An image taken at an angle:
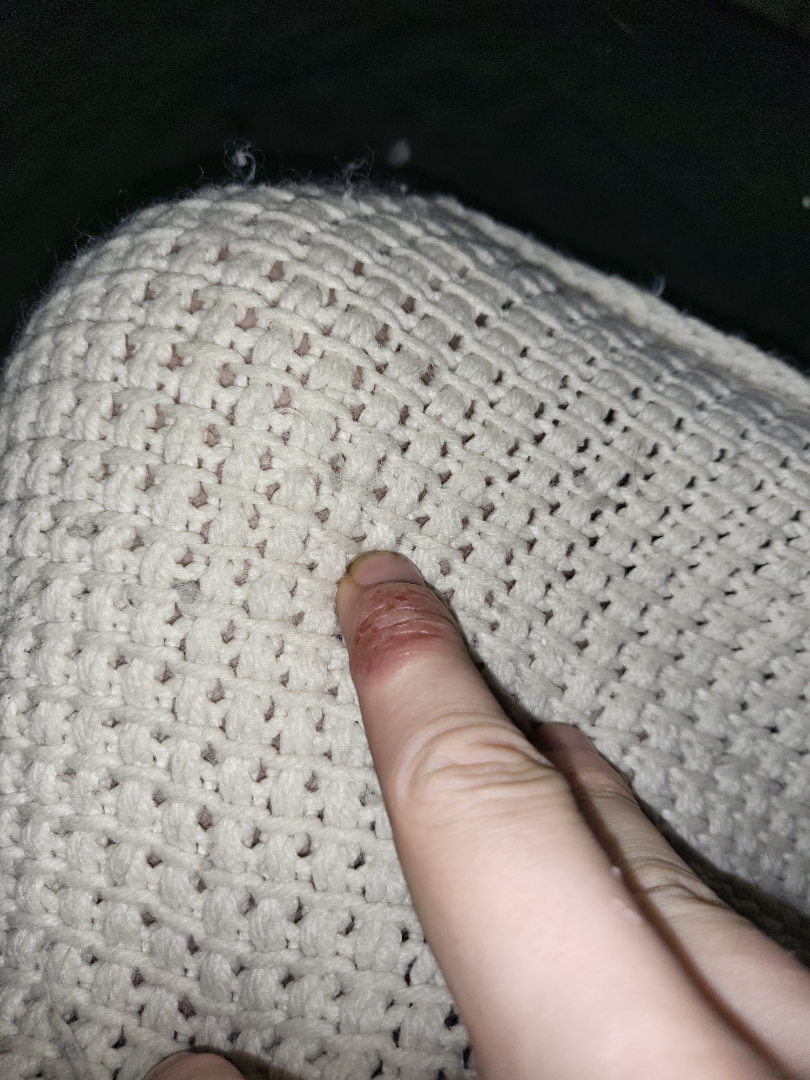Findings:
– assessment — most consistent with Herpes Simplex; also raised was Skin and soft tissue atypical mycobacterial infection; less likely is Allergic Contact Dermatitis